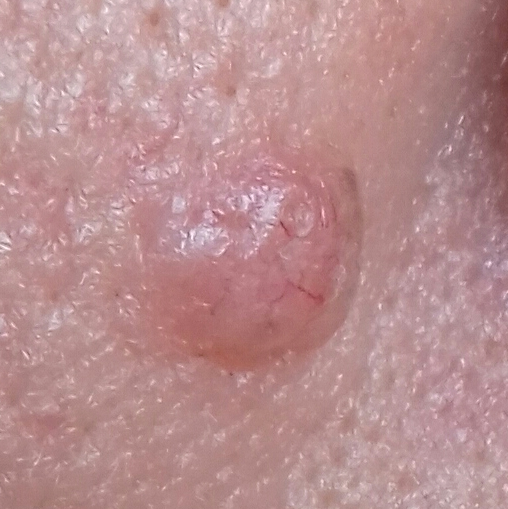Fitzpatrick phototype II.
A clinical close-up photograph of a skin lesion.
A female subject aged 56.
The chart records prior malignancy (patient or family), no pesticide exposure, and no prior skin cancer (patient or family).
Located on the face.
The patient describes that the lesion is elevated, itches, and has grown.
Confirmed on histopathology as a skin cancer — a basal cell carcinoma.